A dermoscopic photograph of a skin lesion:
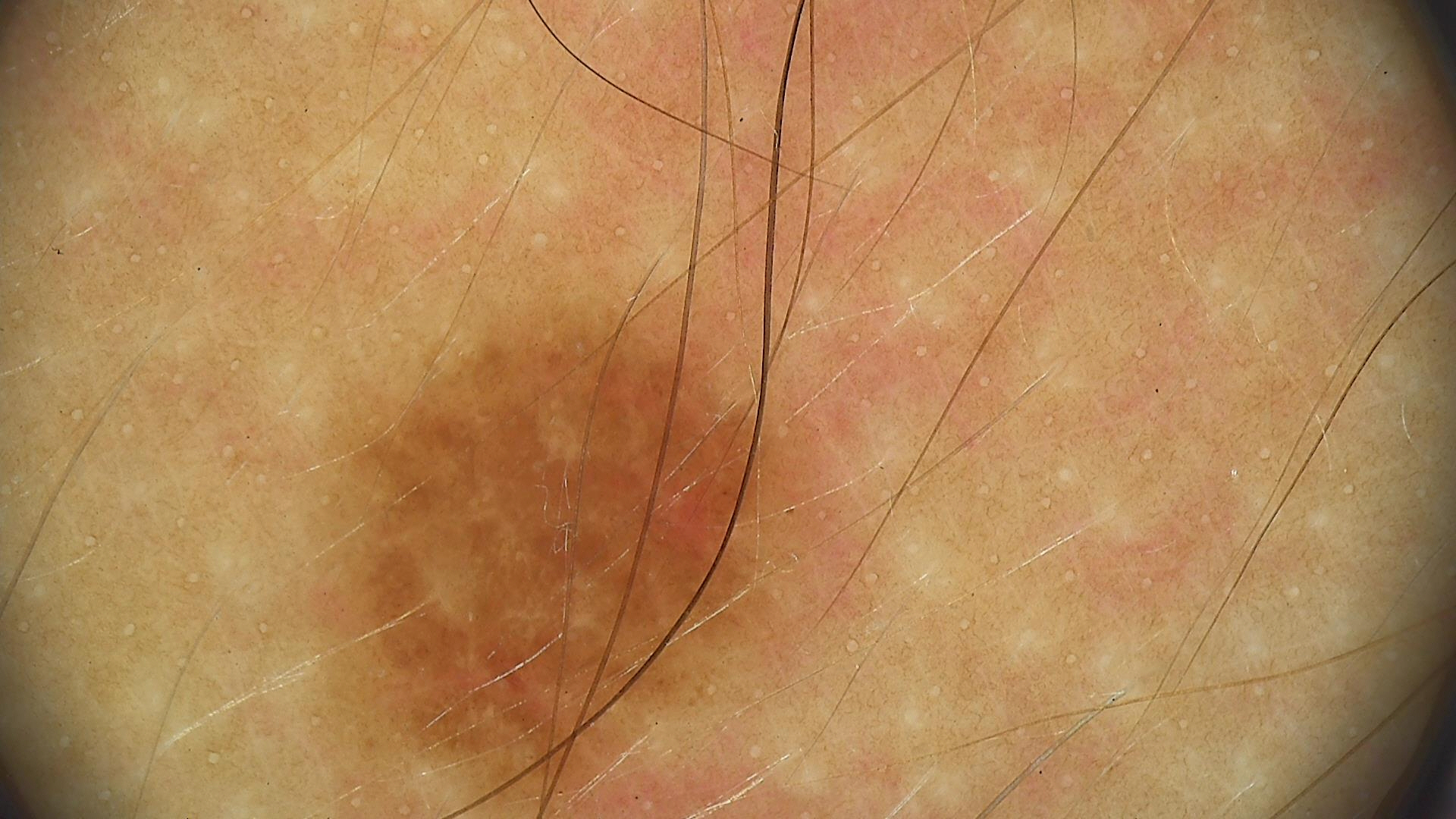class: dysplastic junctional nevus (expert consensus).